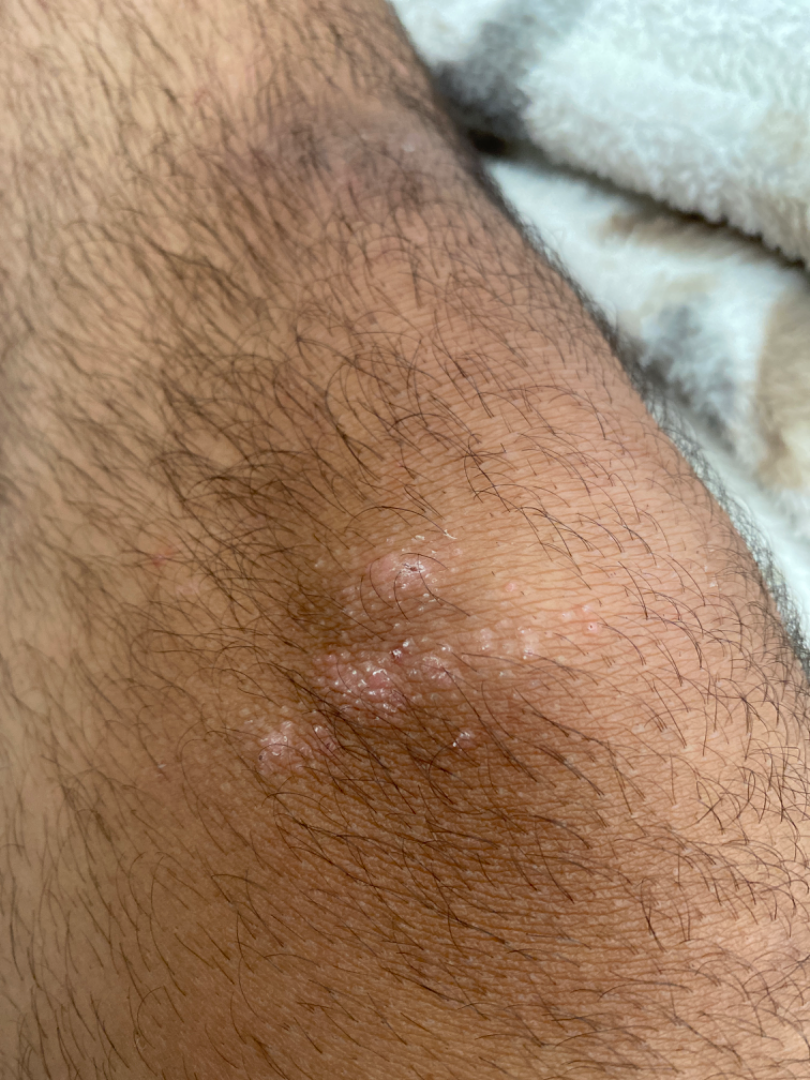{
  "assessment": "indeterminate from the photograph",
  "symptoms": "itching",
  "patient": "male, age 18–29",
  "texture": "raised or bumpy",
  "body_site": "leg",
  "shot_type": "close-up",
  "duration": "three to twelve months"
}